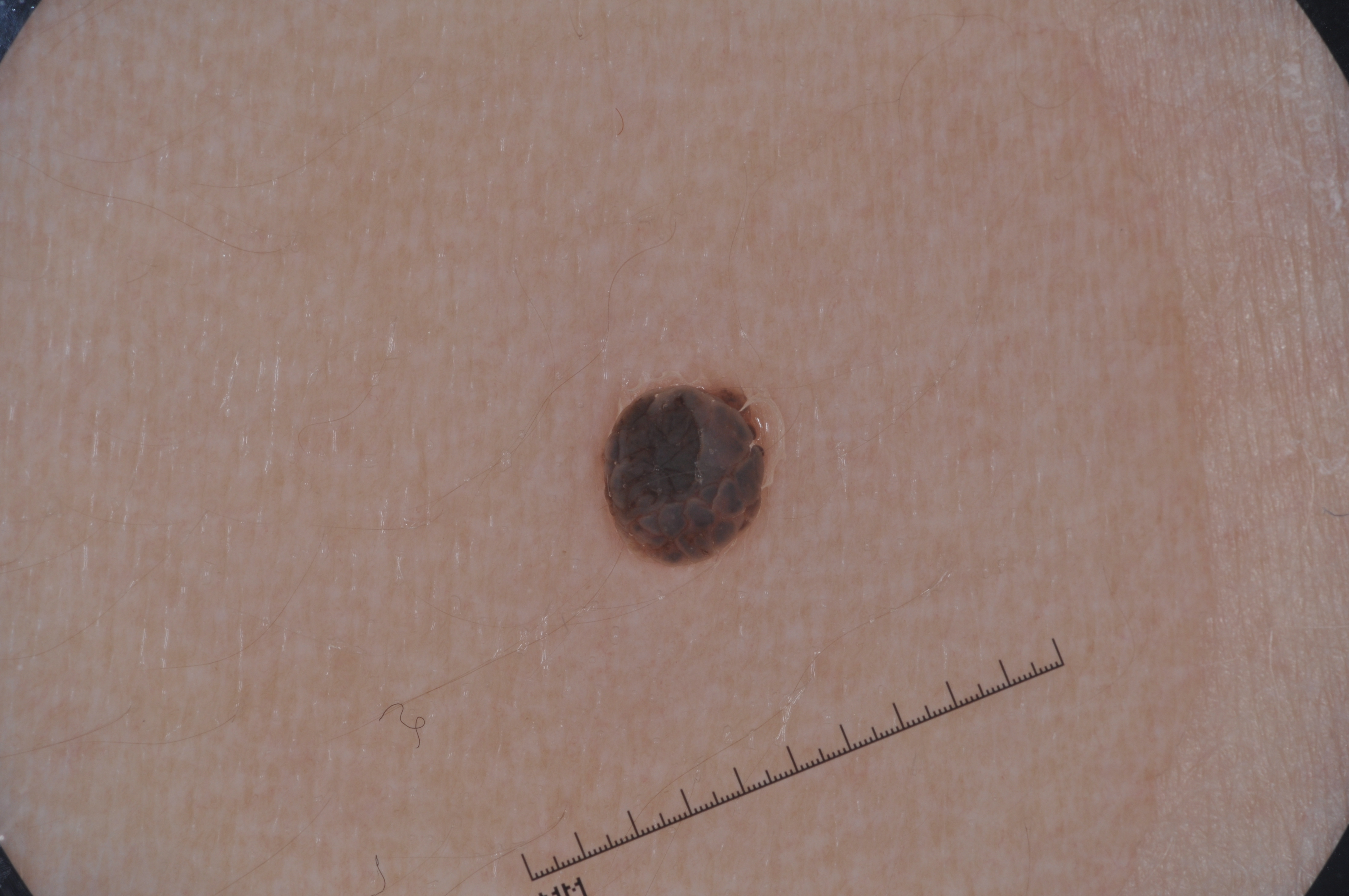{
  "patient": {
    "sex": "female",
    "age_approx": 25
  },
  "image": {
    "modality": "dermoscopy"
  },
  "lesion_extent": "small",
  "lesion_location": {
    "bbox_xyxy": [
      593,
      379,
      773,
      567
    ]
  },
  "dermoscopic_features": {
    "present": [],
    "absent": [
      "pigment network",
      "milia-like cysts",
      "negative network",
      "streaks"
    ]
  },
  "diagnosis": {
    "name": "melanocytic nevus",
    "malignancy": "benign",
    "lineage": "melanocytic",
    "provenance": "clinical"
  }
}